The affected area is the arm, leg and back of the hand; the contributor is female; the photo was captured at an angle:
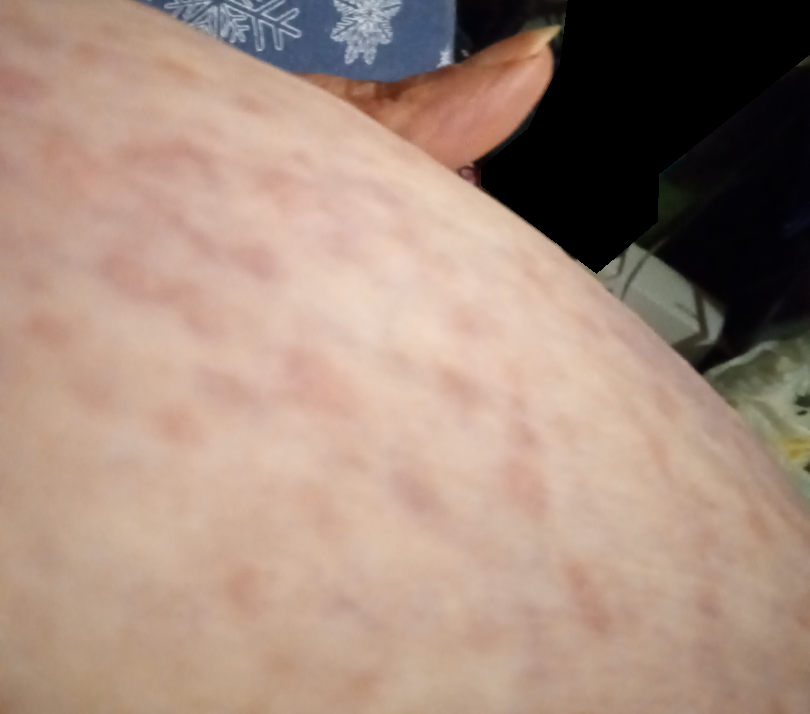The skin findings could not be characterized from the image.